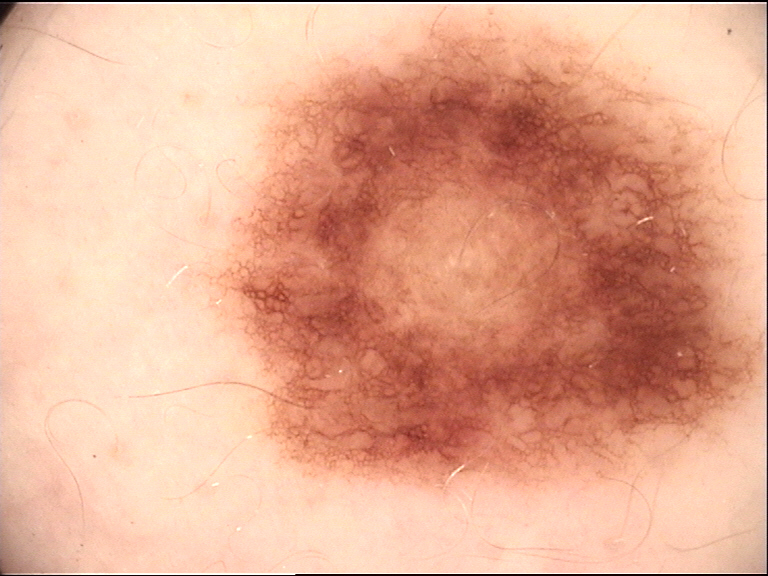{"diagnosis": {"name": "dysplastic junctional nevus", "code": "jd", "malignancy": "benign", "super_class": "melanocytic", "confirmation": "expert consensus"}}